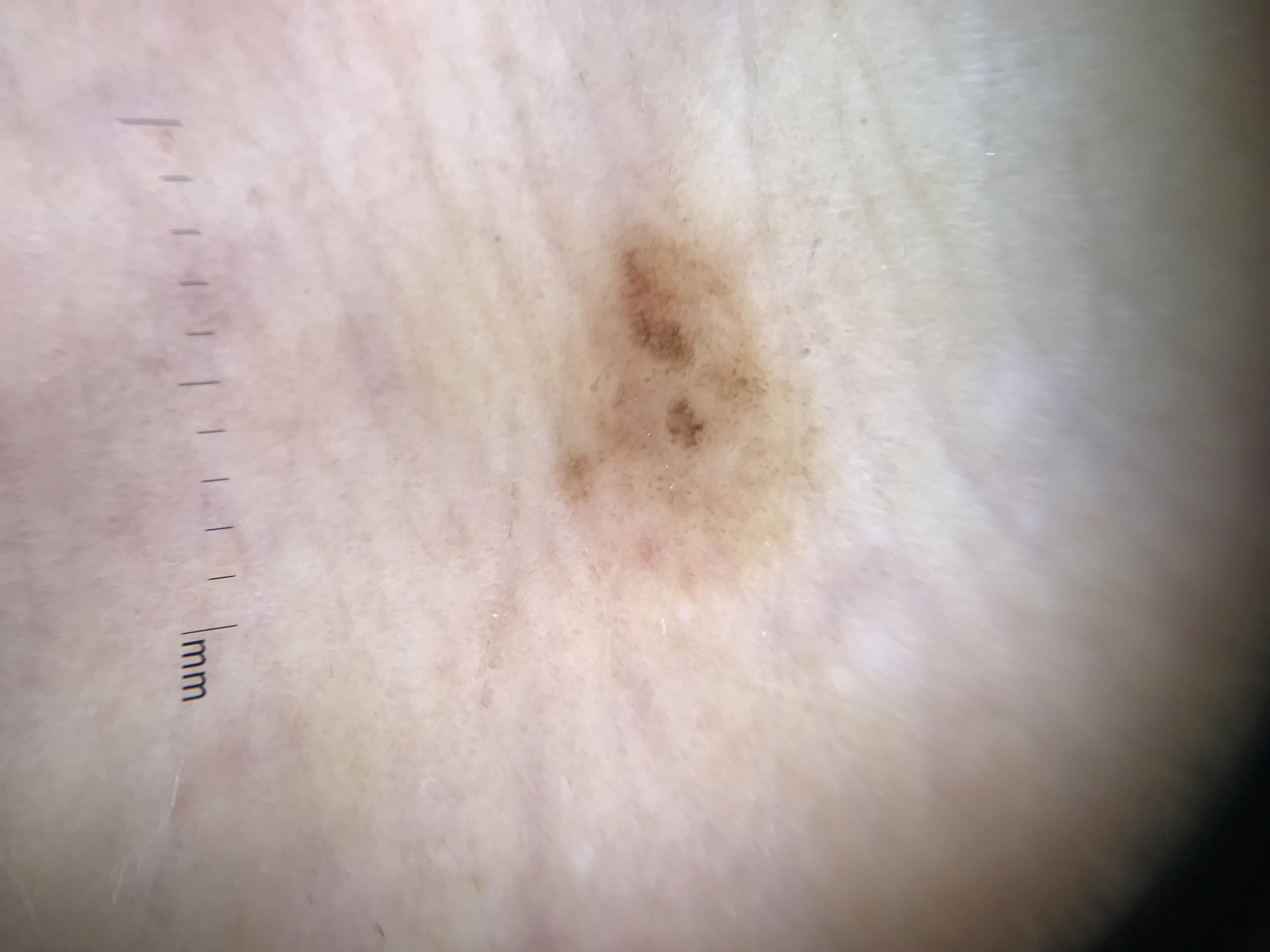A dermoscopic close-up of a skin lesion. The morphology is that of a banal lesion. Classified as an acral compound nevus.